A female subject aged around 80. A skin lesion imaged with a dermatoscope.
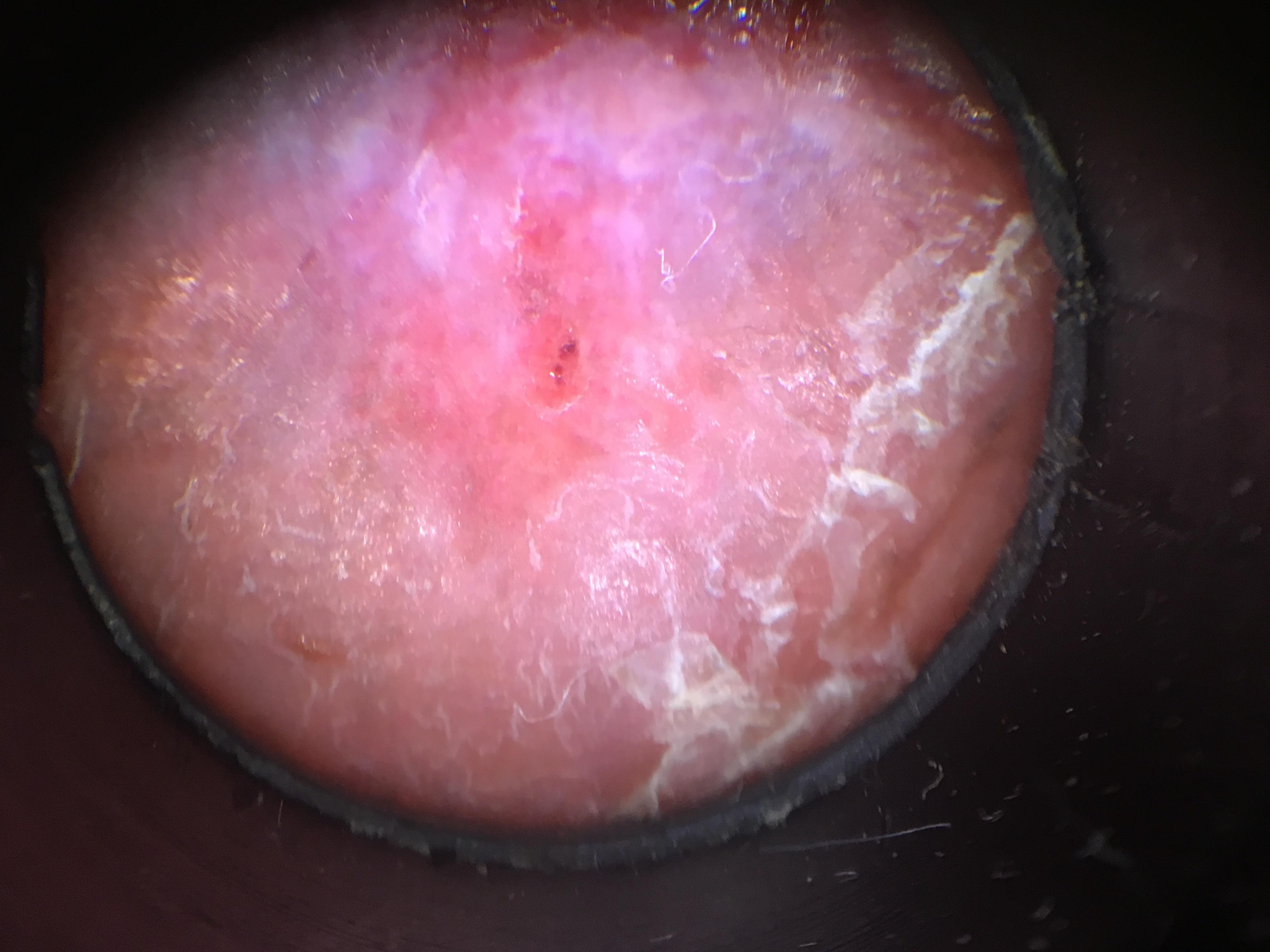<lesion>
<diagnosis>
<name>Basal cell carcinoma</name>
<malignancy>malignant</malignancy>
<confirmation>histopathology</confirmation>
<lineage>adnexal</lineage>
</diagnosis>
</lesion>